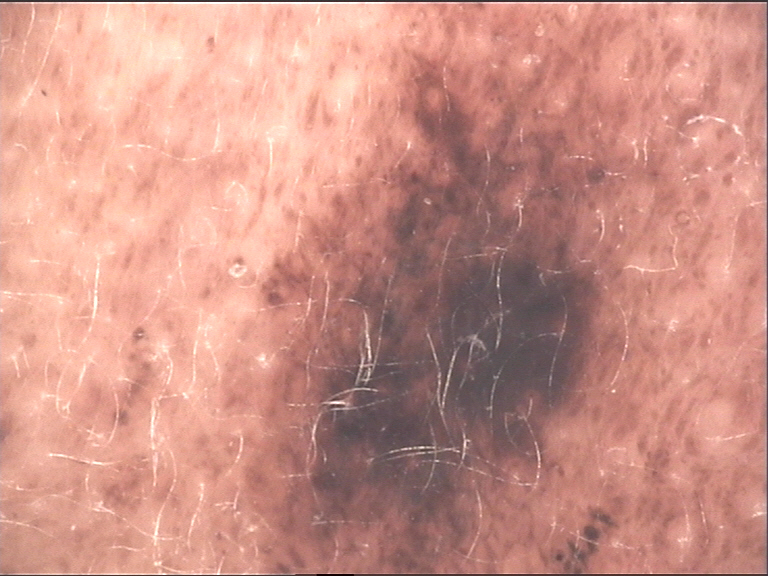{
  "diagnosis": {
    "name": "congenital compound nevus",
    "code": "ccb",
    "malignancy": "benign",
    "super_class": "melanocytic",
    "confirmation": "expert consensus"
  }
}